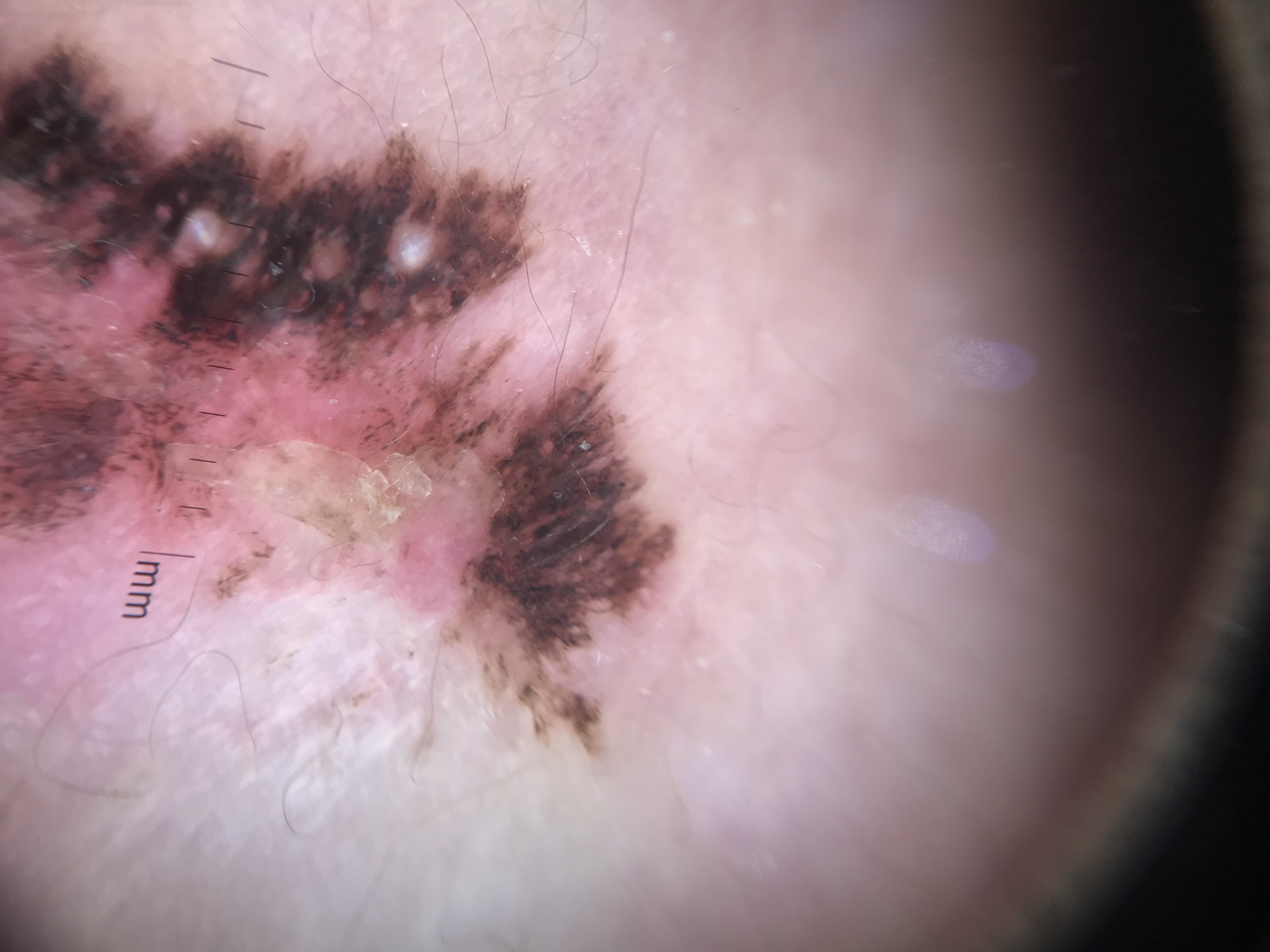diagnosis: melanoma (biopsy-proven).